The condition has been present for less than one week, this is a close-up image, associated systemic symptoms include joint pain, the patient considered this a rash, the lesion is described as flat and rough or flaky:
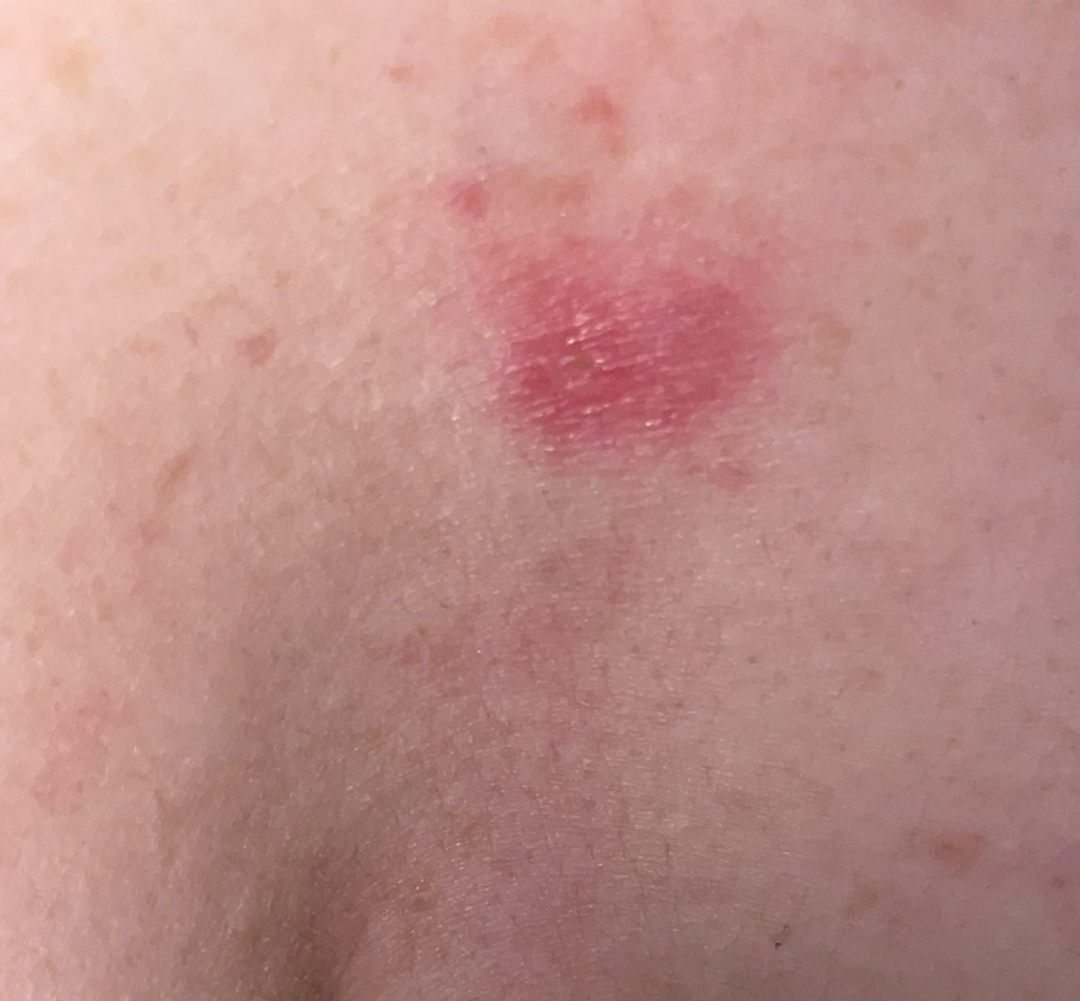Notes:
* assessment · unable to determine